A dermoscopic close-up of a skin lesion:
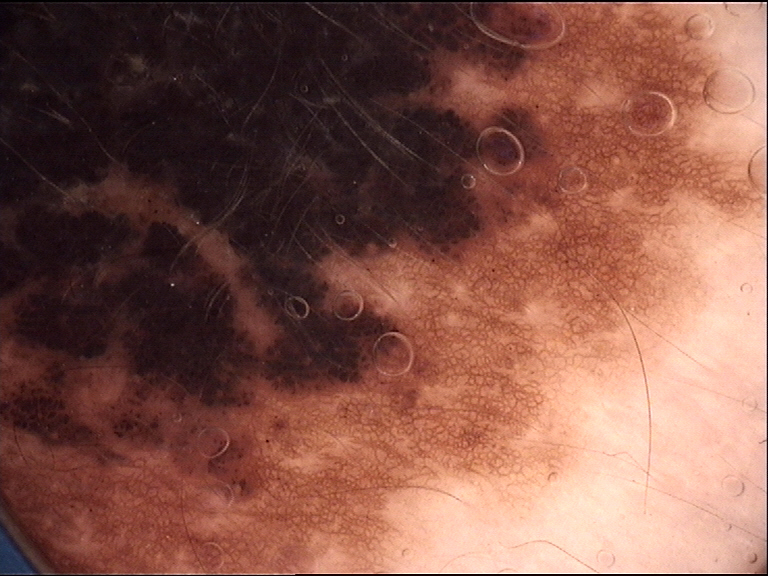Classified as a banal lesion — a congenital compound nevus.